The patient notes the condition has been present for about one day · no associated lesion symptoms were reported · the photograph was taken at a distance · the patient notes the lesion is raised or bumpy · located on the front of the torso:
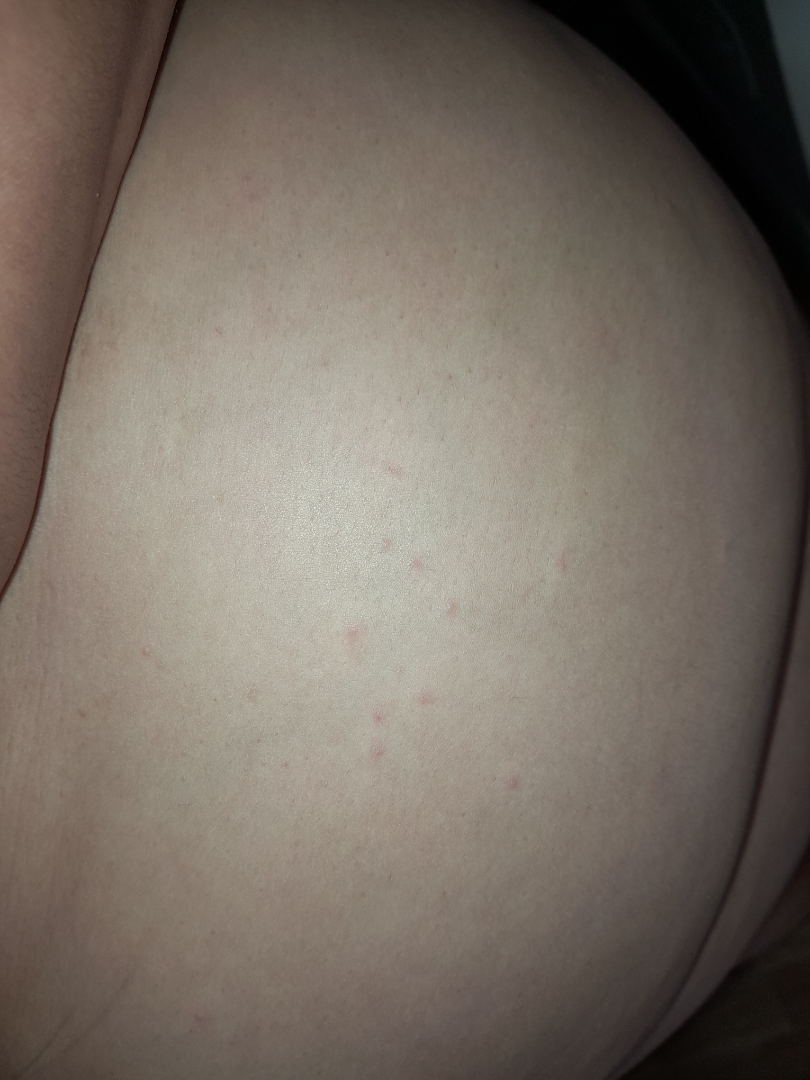Diagnostic features were not clearly distinguishable in this photograph.